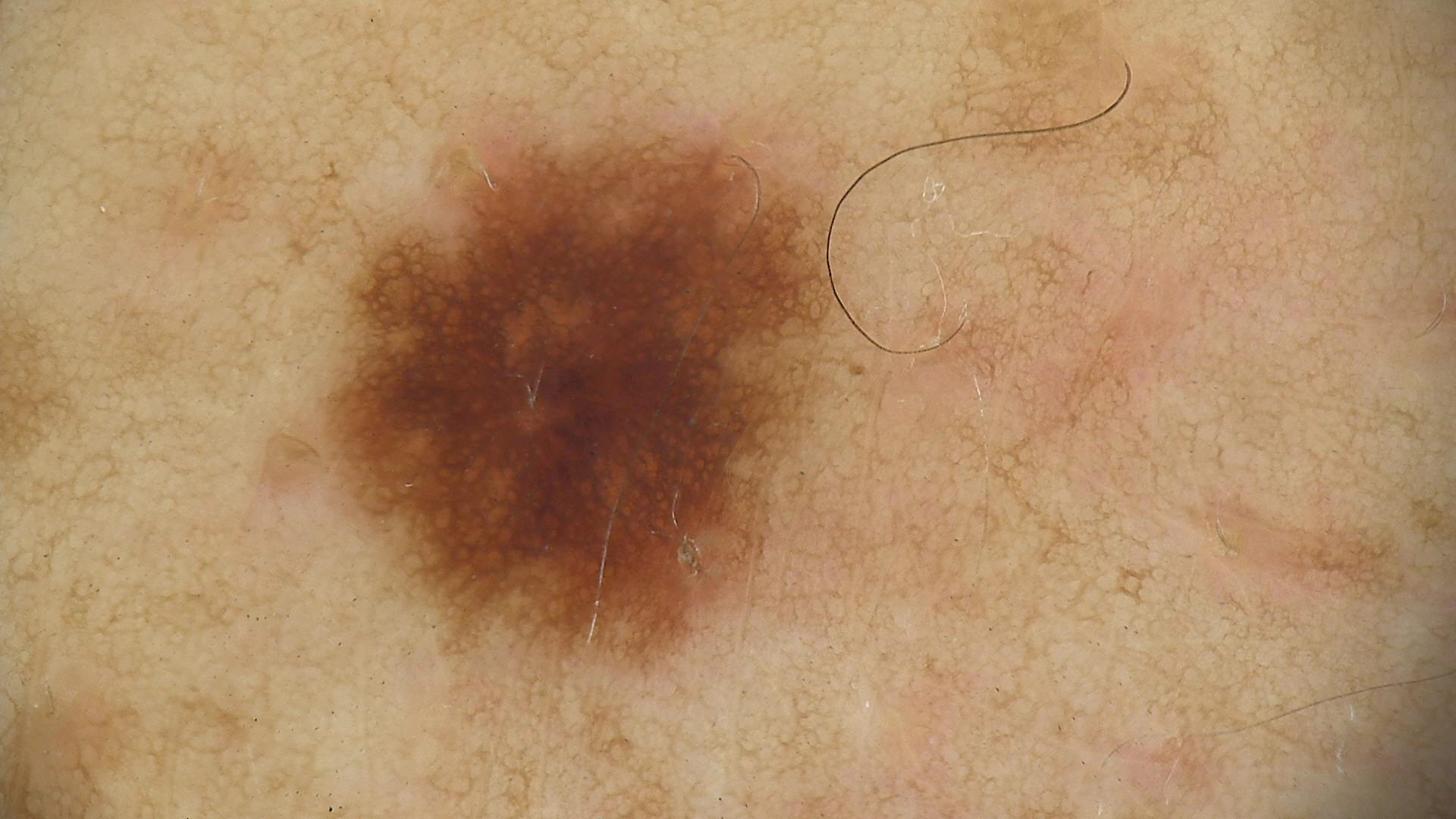A dermoscopy image of a single skin lesion. Labeled as a dysplastic junctional nevus.